A dermoscopy image of a single skin lesion; a male patient in their mid- to late 30s — 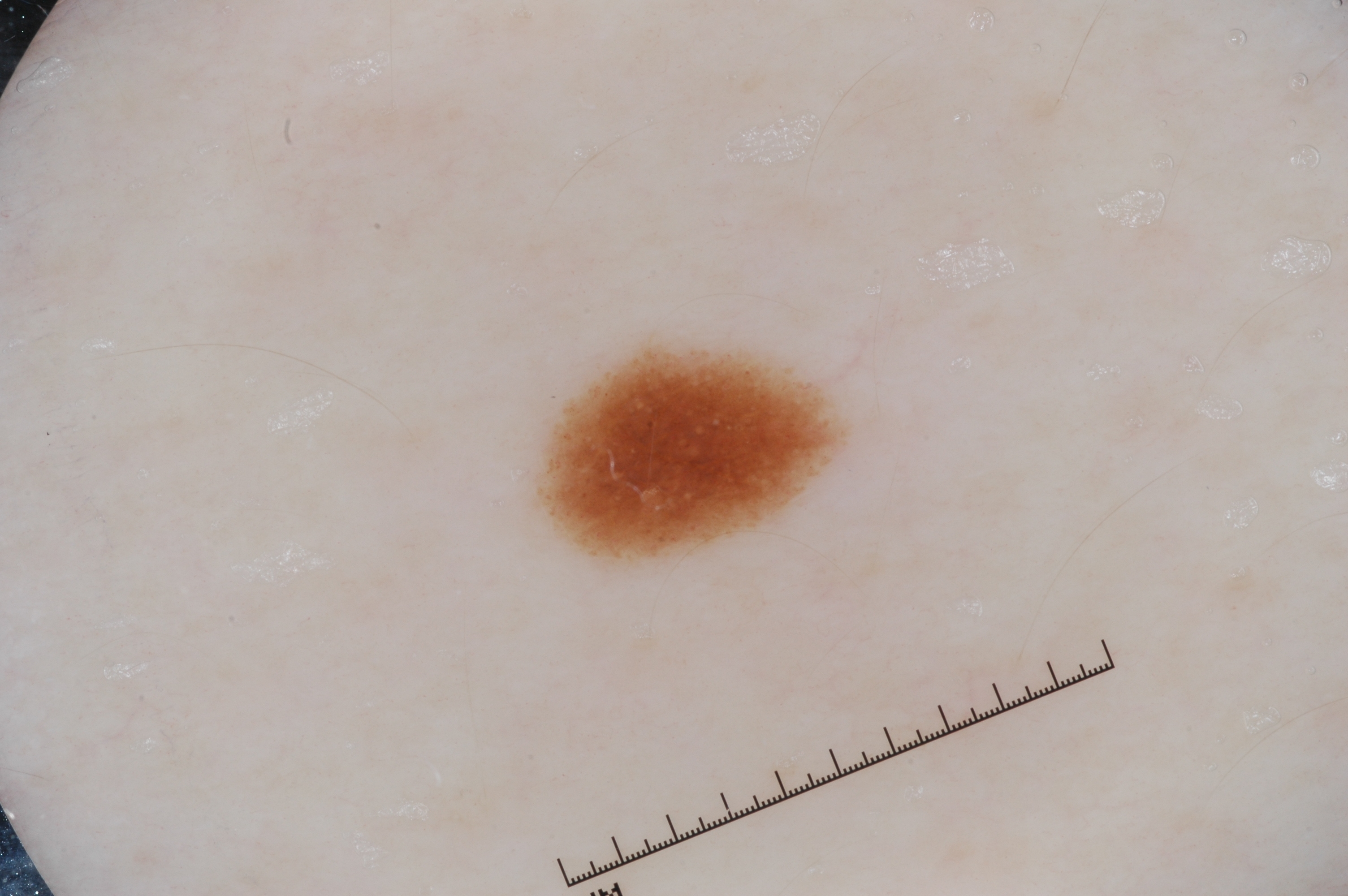{
  "lesion_extent": "small",
  "lesion_location": {
    "bbox_xyxy": [
      537,
      343,
      842,
      560
    ]
  },
  "dermoscopic_features": {
    "present": [],
    "absent": [
      "streaks",
      "pigment network",
      "negative network",
      "milia-like cysts"
    ]
  },
  "diagnosis": {
    "name": "melanocytic nevus",
    "malignancy": "benign",
    "lineage": "melanocytic",
    "provenance": "clinical"
  }
}